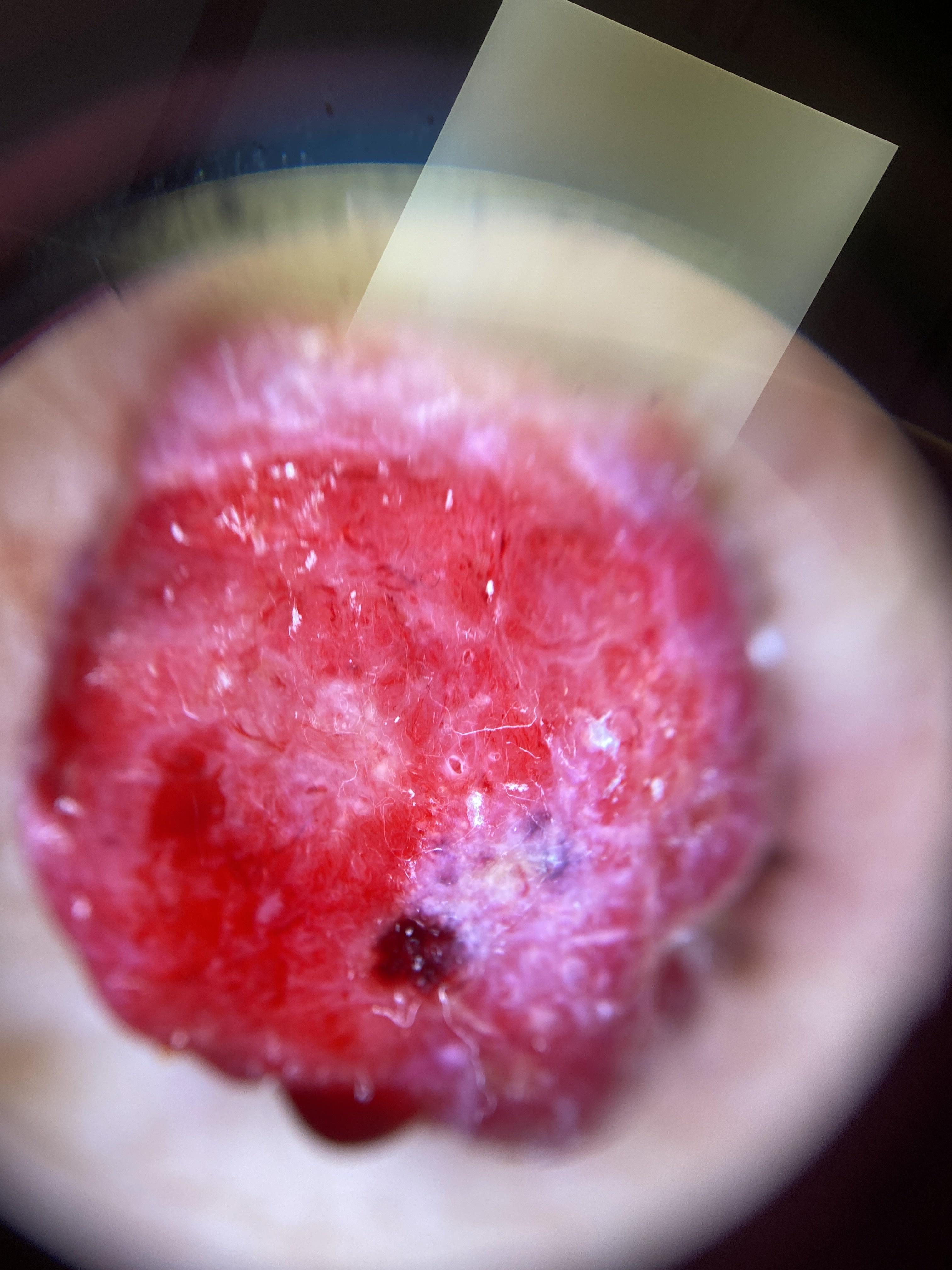FST=II | patient=female, approximately 80 years of age | diagnostic label=Melanoma (biopsy-proven).